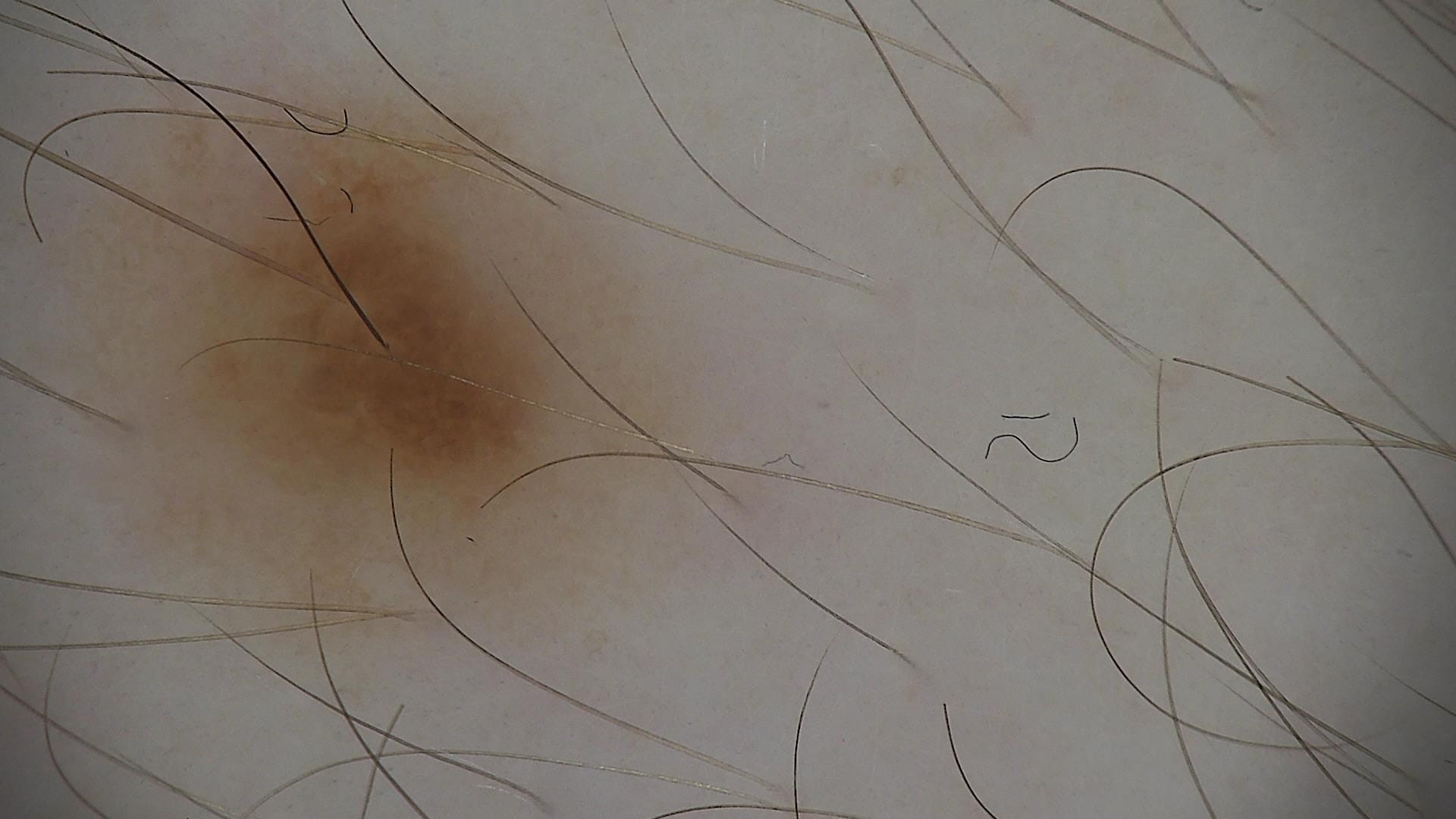modality — dermoscopy; assessment — dysplastic junctional nevus (expert consensus).